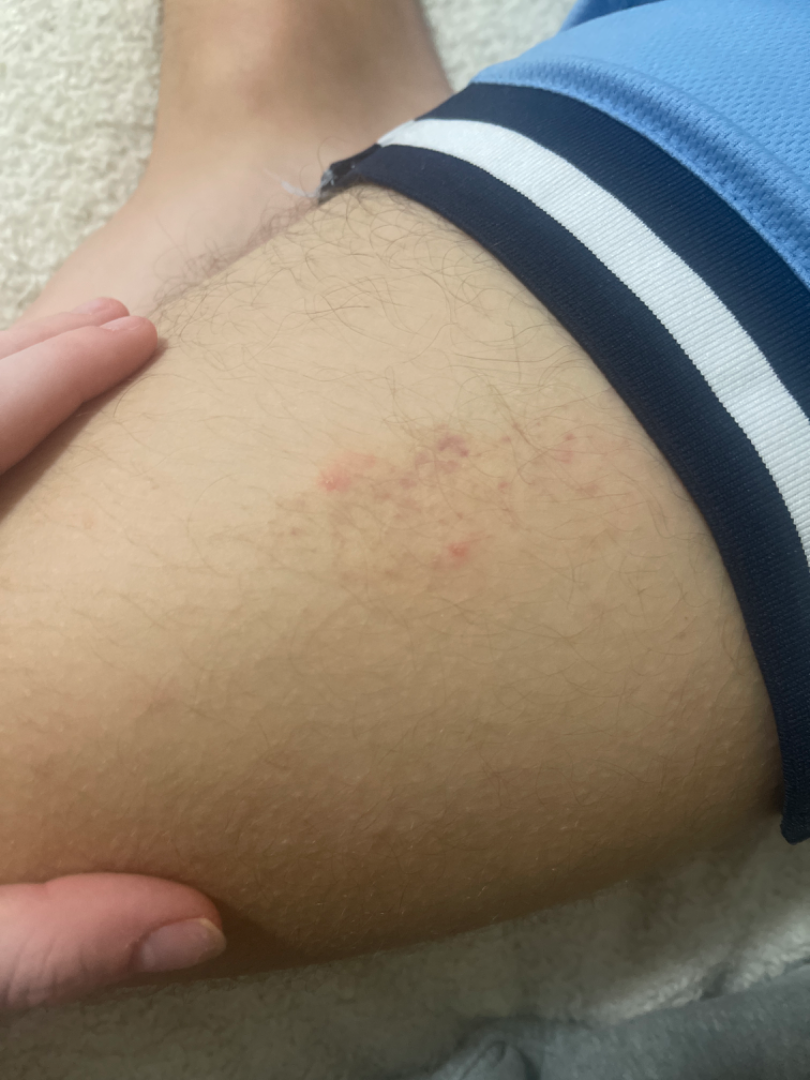Present for about one day. The lesion is described as raised or bumpy. The leg is involved. This is a close-up image. The reviewing clinician's impression was: Folliculitis, ecchymoses and Post-Inflammatory hyperpigmentation were considered with similar weight.